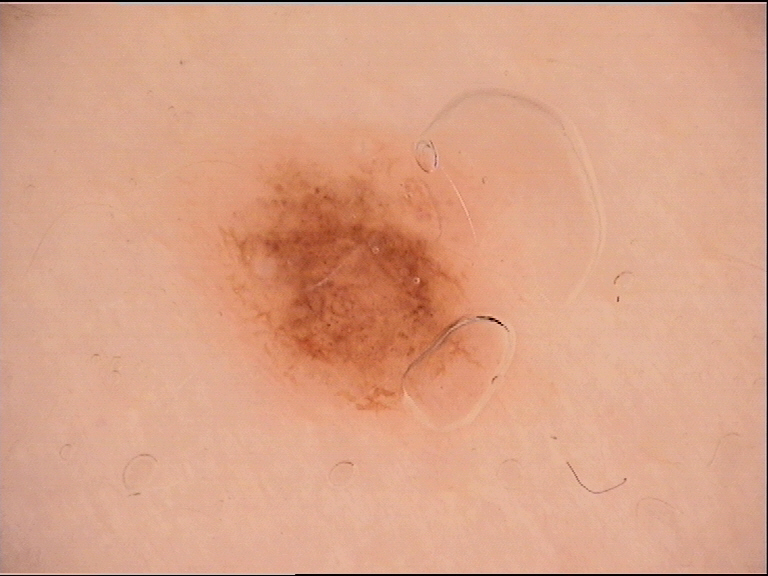image type — dermatoscopy; class — dysplastic junctional nevus (expert consensus).